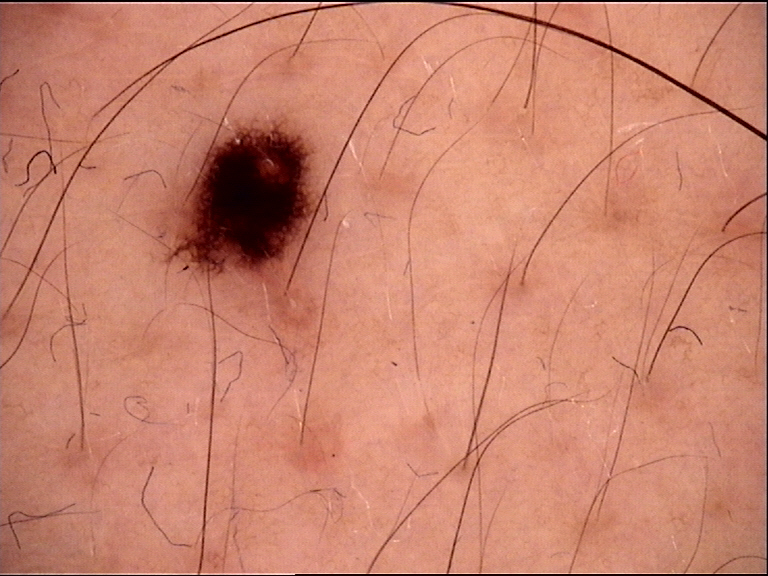A dermoscopic image of a skin lesion. The architecture is that of a banal lesion. Labeled as a junctional nevus.